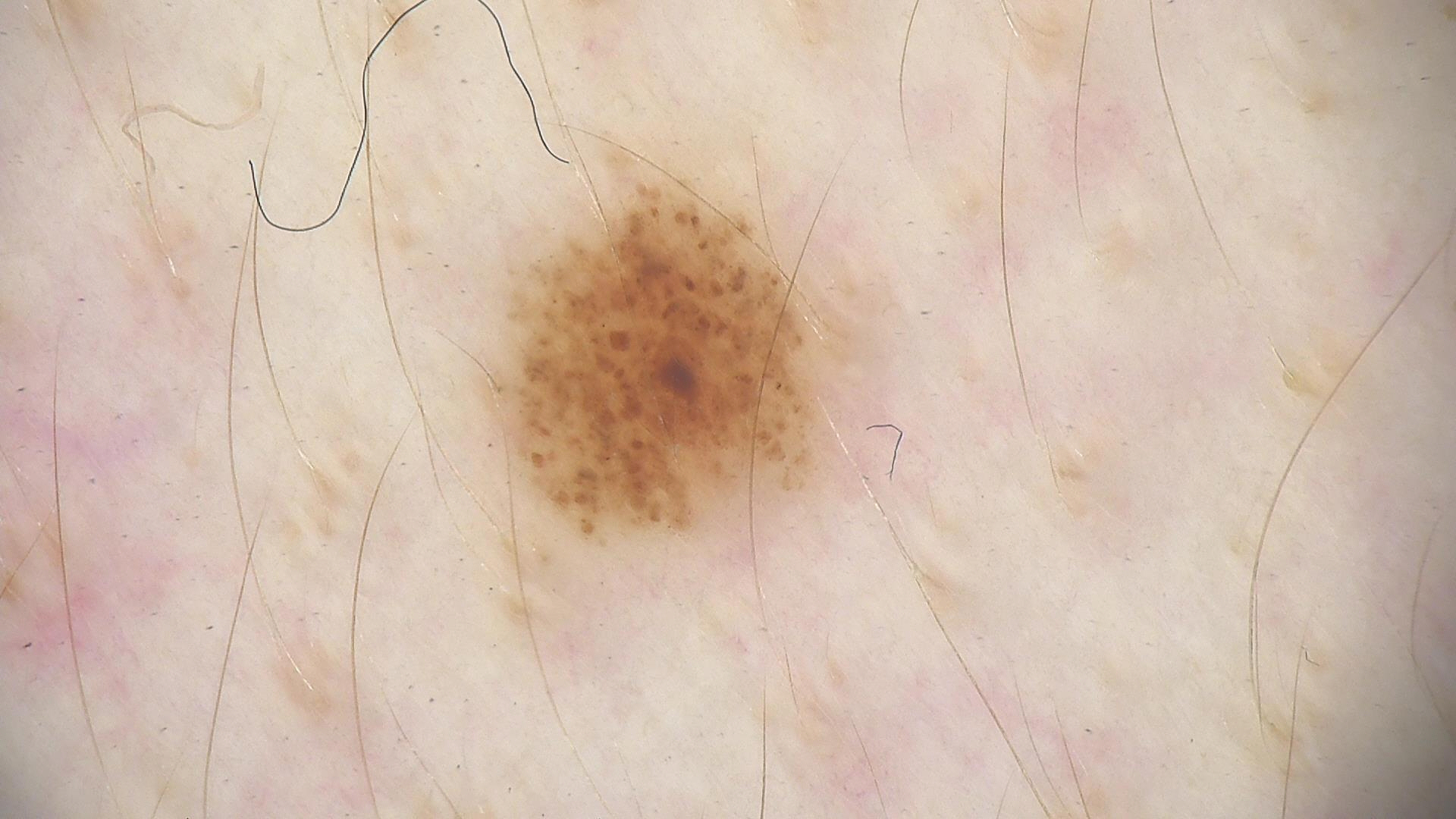diagnosis:
  name: dysplastic junctional nevus
  code: jd
  malignancy: benign
  super_class: melanocytic
  confirmation: expert consensus